A male subject age 50:
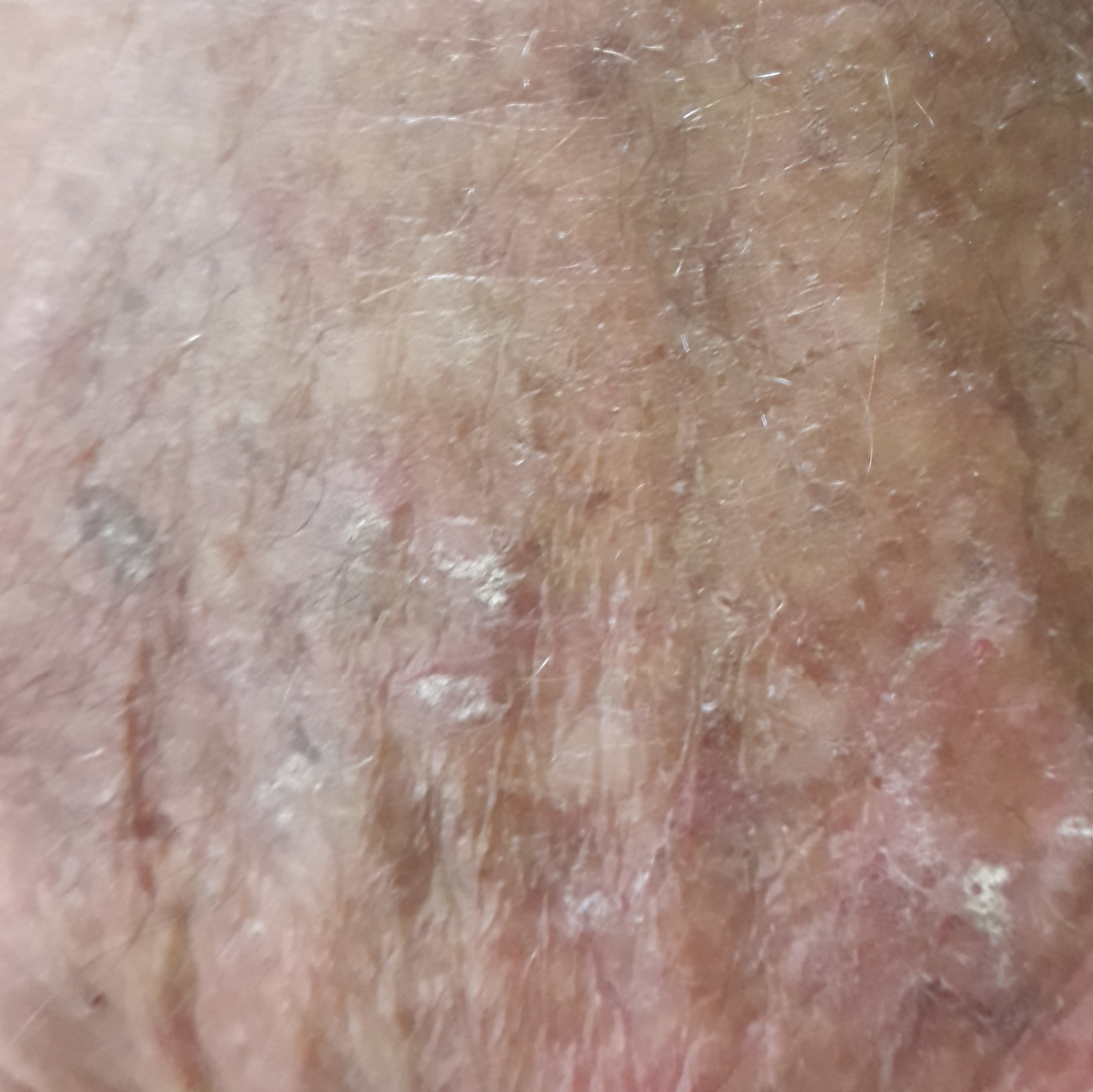  lesion_location: a hand
  symptoms:
    present:
      - elevation
      - itching
    absent:
      - pain
      - change in appearance
  diagnosis:
    name: actinic keratosis
    code: ACK
    malignancy: indeterminate
    confirmation: clinical consensus